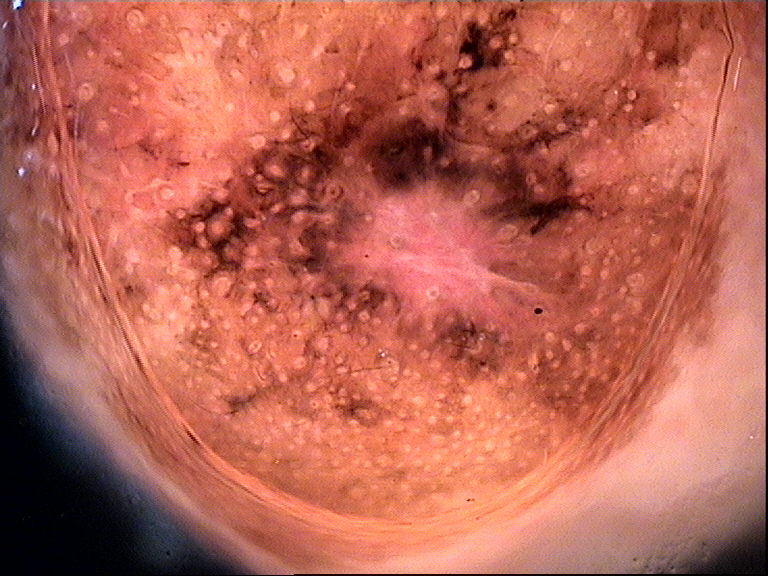imaging — dermoscopy
diagnostic label — lentigo maligna (biopsy-proven)